Fitzpatrick IV; a male subject 81 years of age — 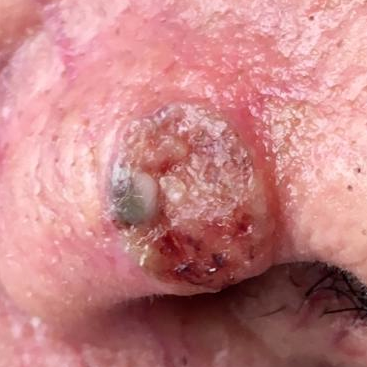Q: How large is the lesion?
A: 10x7 mm
Q: What does the patient describe?
A: itching, pain, elevation, bleeding, growth
Q: What did the workup show?
A: basal cell carcinoma (biopsy-proven)